This image was taken at an angle.
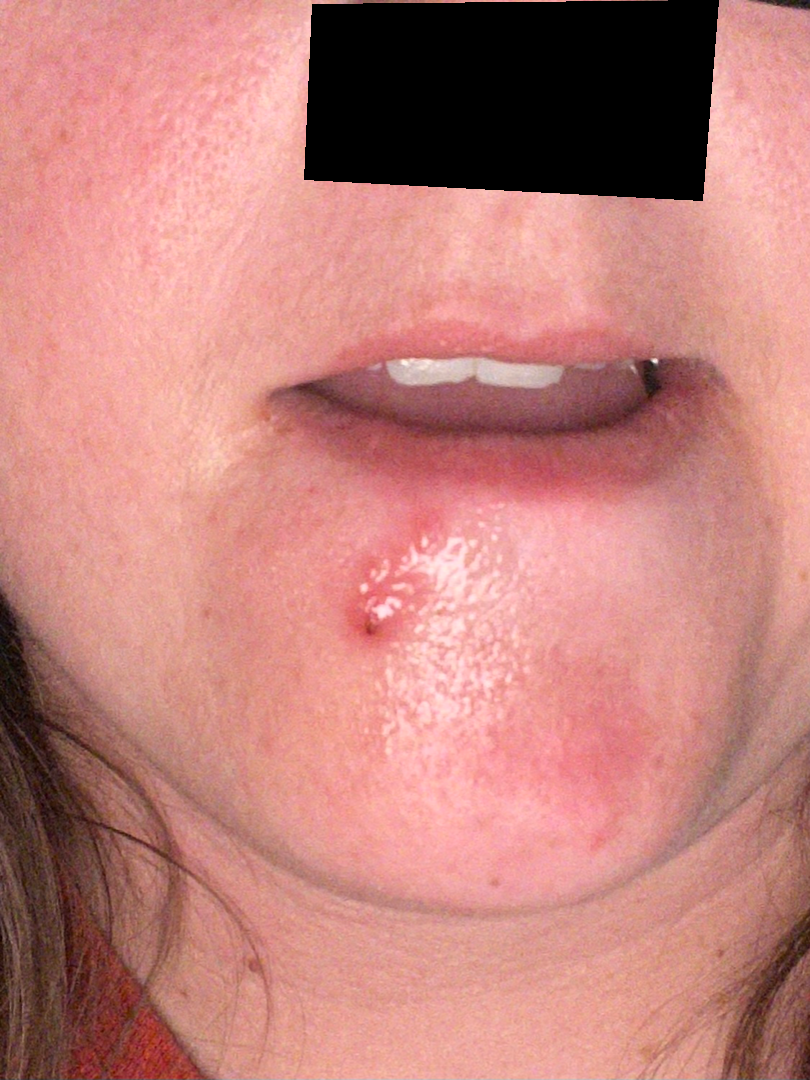| field | value |
|---|---|
| diagnostic considerations | Herpes Simplex (0.54); Photodermatitis (0.23); Irritant Contact Dermatitis (0.23) |